A skin lesion imaged with a dermatoscope — 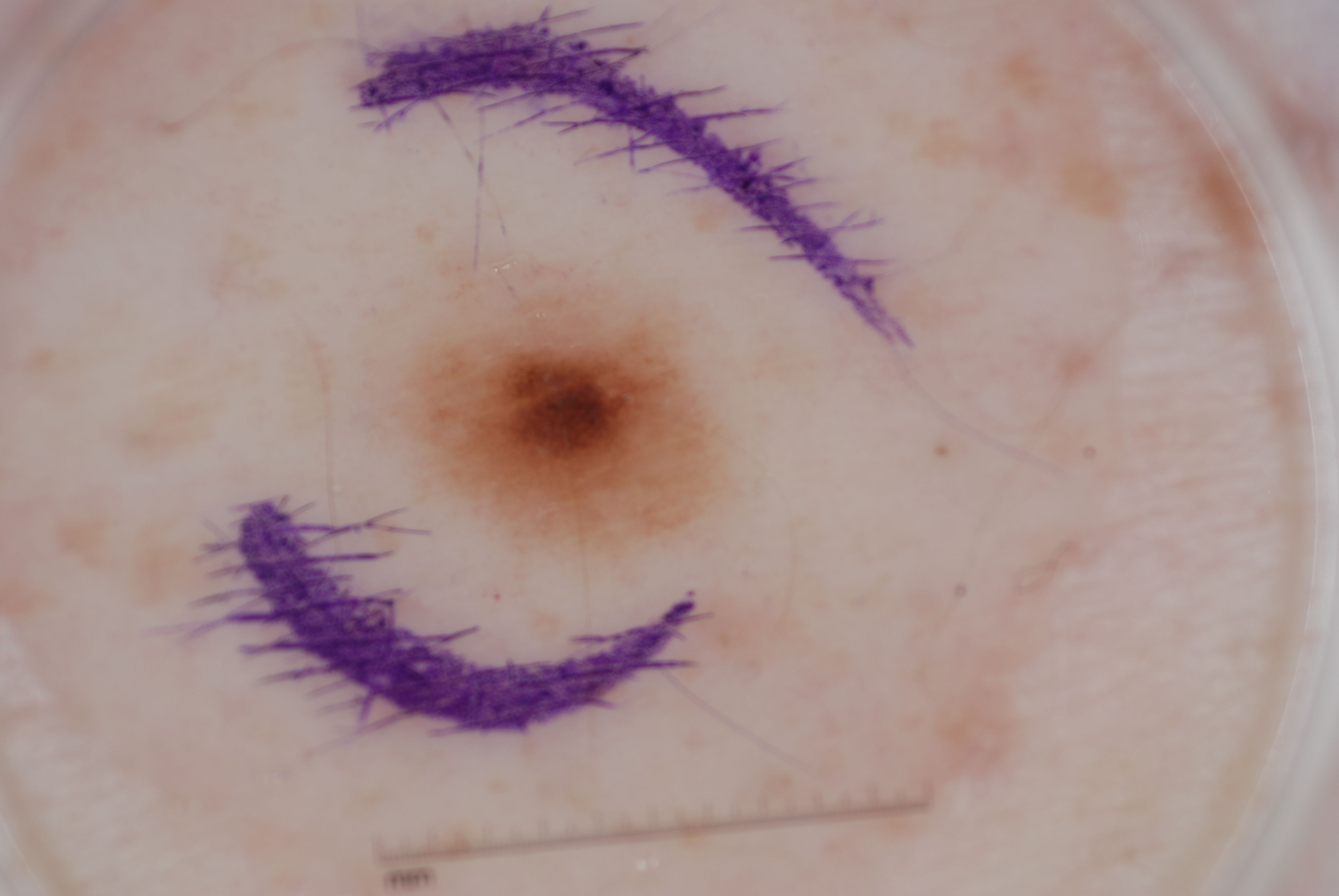| feature | finding |
|---|---|
| absent dermoscopic findings | streaks, pigment network, negative network, and milia-like cysts |
| bounding box | x1=398 y1=273 x2=722 y2=553 |
| diagnosis | a melanocytic nevus |